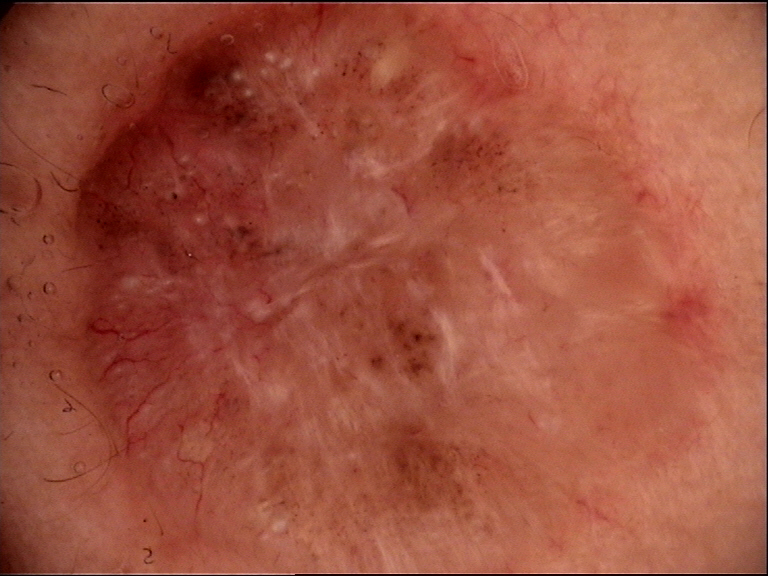* image type — dermatoscopy
* lesion type — keratinocytic
* label — basal cell carcinoma (biopsy-proven)